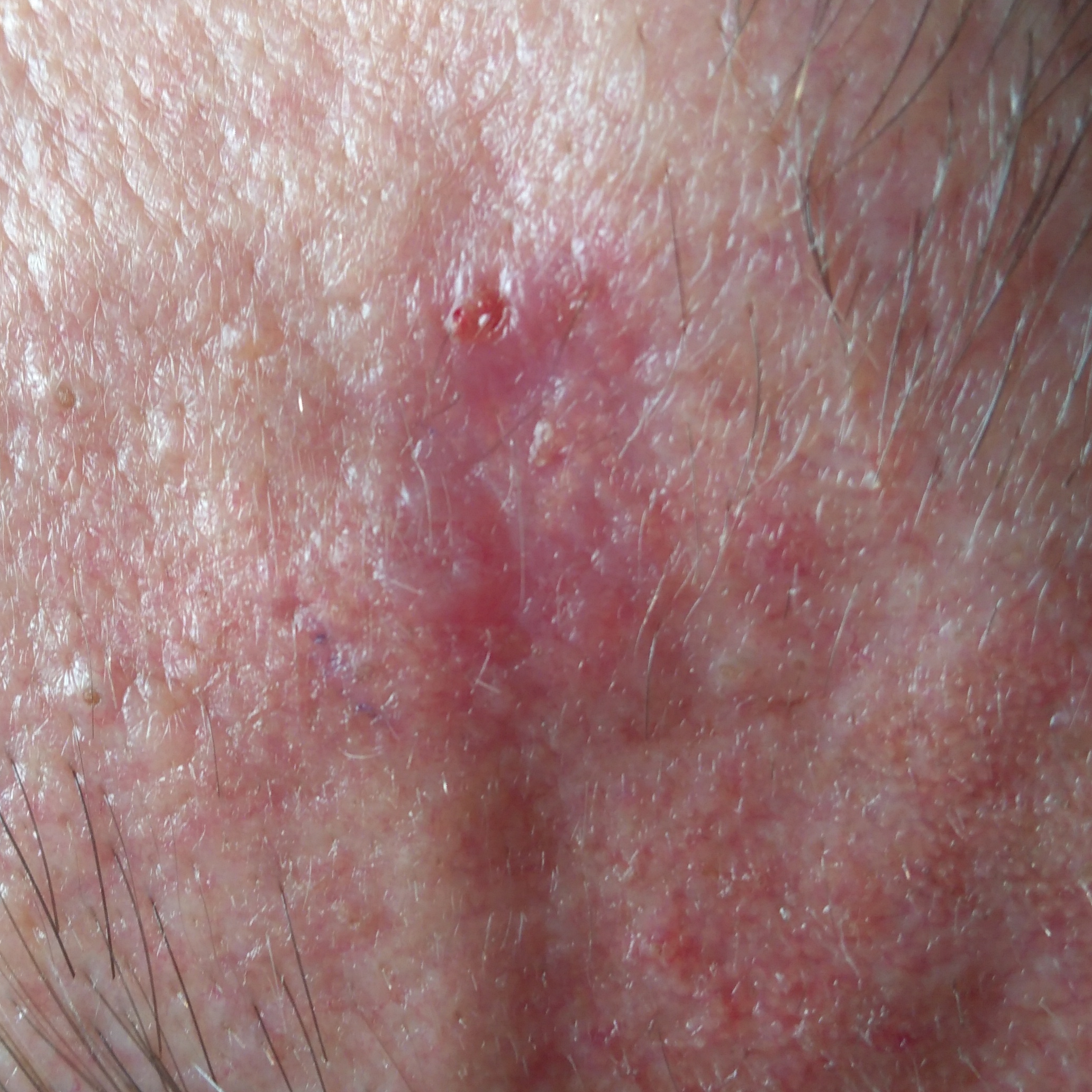Q: Tell me about the patient.
A: male, in their mid-50s
Q: What did the workup show?
A: basal cell carcinoma (biopsy-proven)